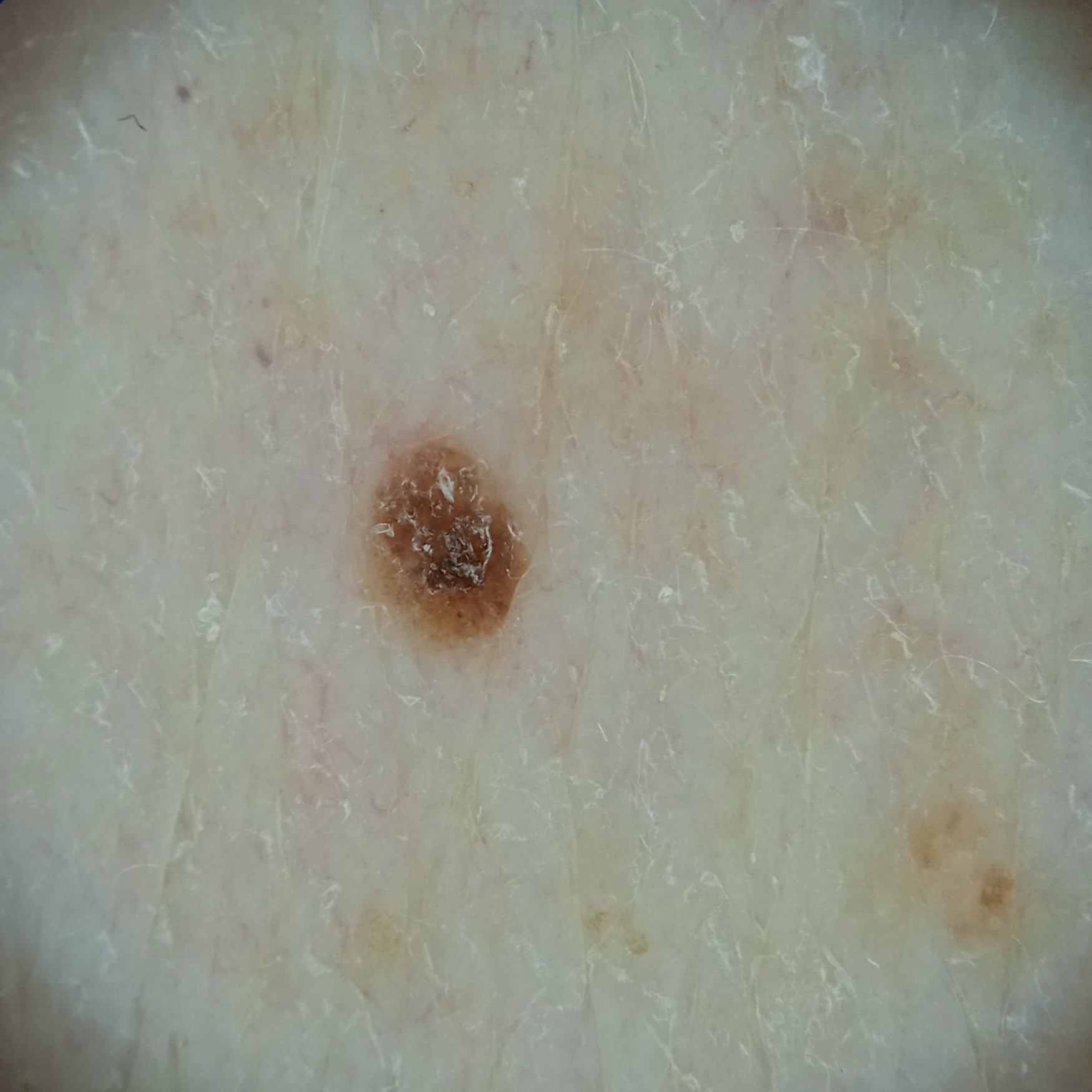A male subject age 83. A dermatoscopic image of a skin lesion. The lesion is on the back. Measuring roughly 2.5 mm. Reviewed by four dermatologists, the consensus diagnosis was a seborrheic keratosis; there was some disagreement among the reviewers.